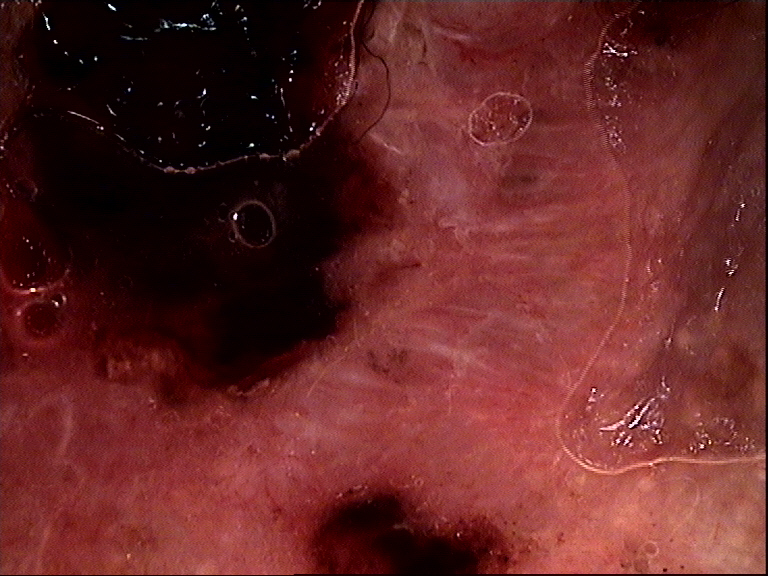Summary:
A dermatoscopic image of a skin lesion.
Diagnosis:
Confirmed on histopathology as a keratinocytic, malignant lesion — a basal cell carcinoma.